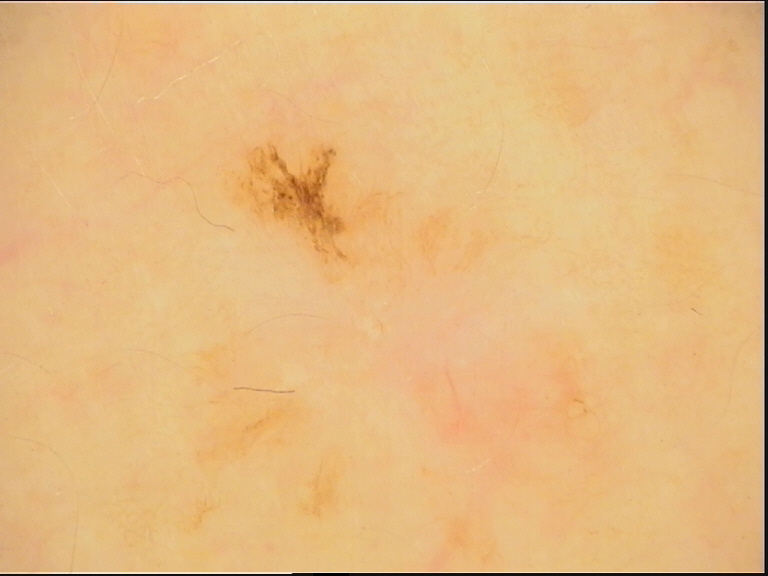image: dermatoscopy
diagnosis:
  name: dysplastic junctional nevus
  code: jd
  malignancy: benign
  super_class: melanocytic
  confirmation: expert consensus